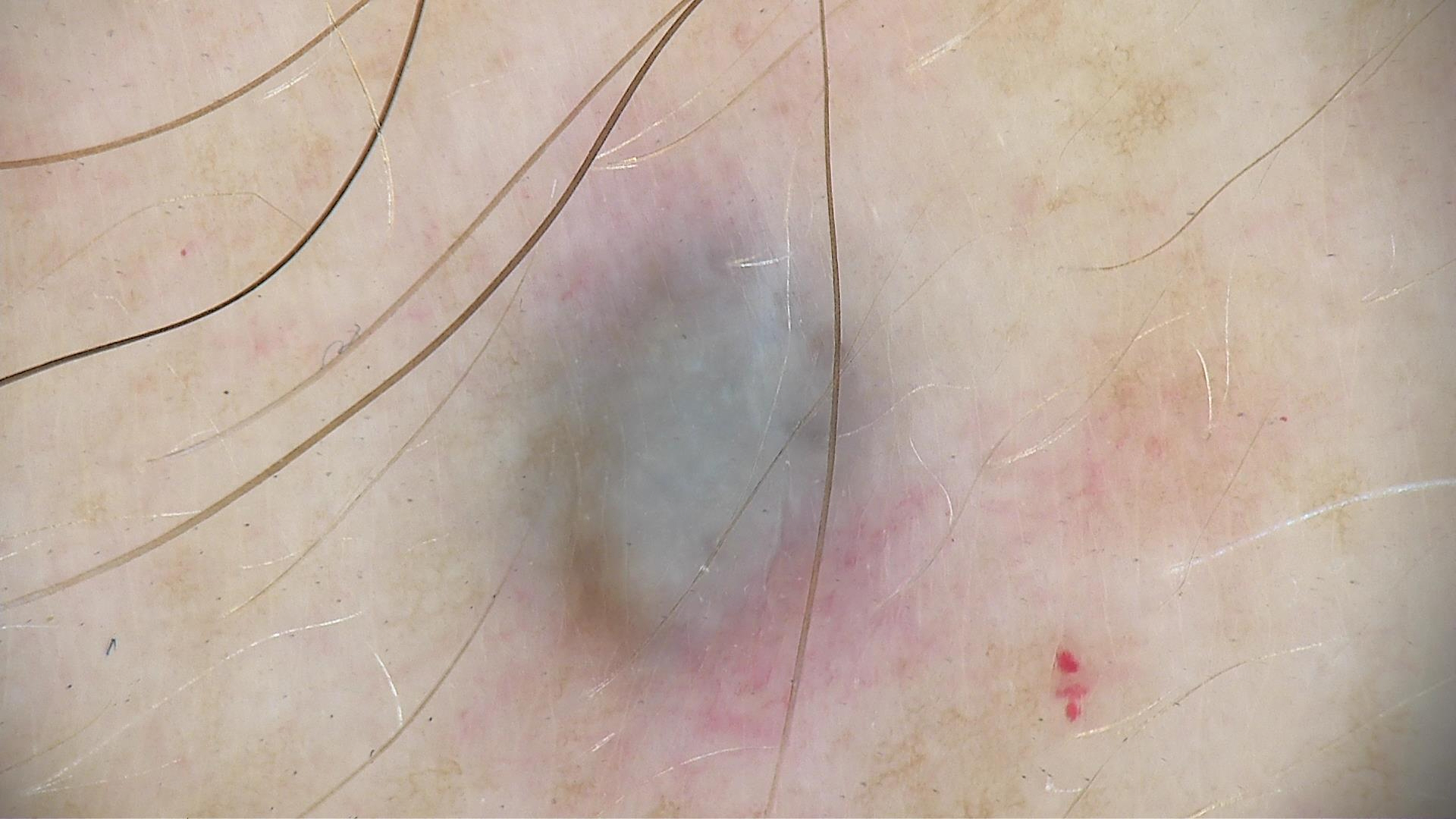A dermoscopic image of a skin lesion.
Labeled as a banal lesion — a blue nevus.